A dermatoscopic image of a skin lesion.
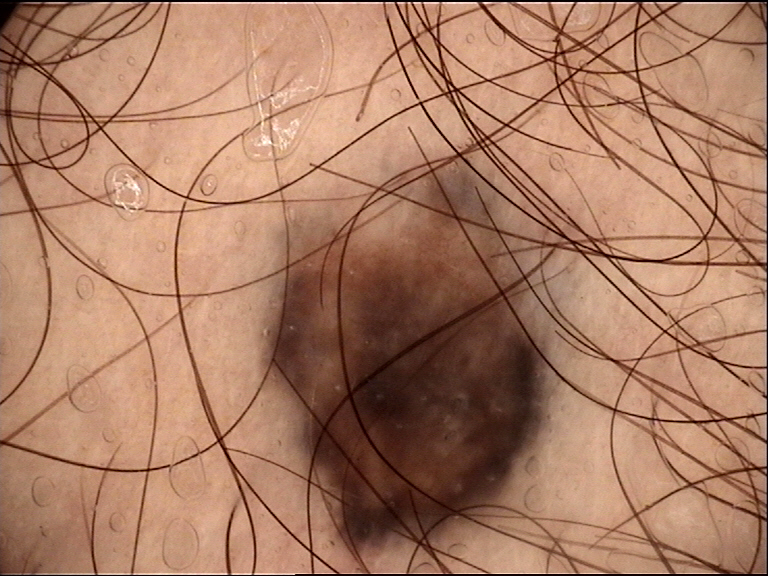{"diagnosis": {"name": "blue nevus", "code": "bdb", "malignancy": "benign", "super_class": "melanocytic", "confirmation": "expert consensus"}}